The photo was captured at an angle — 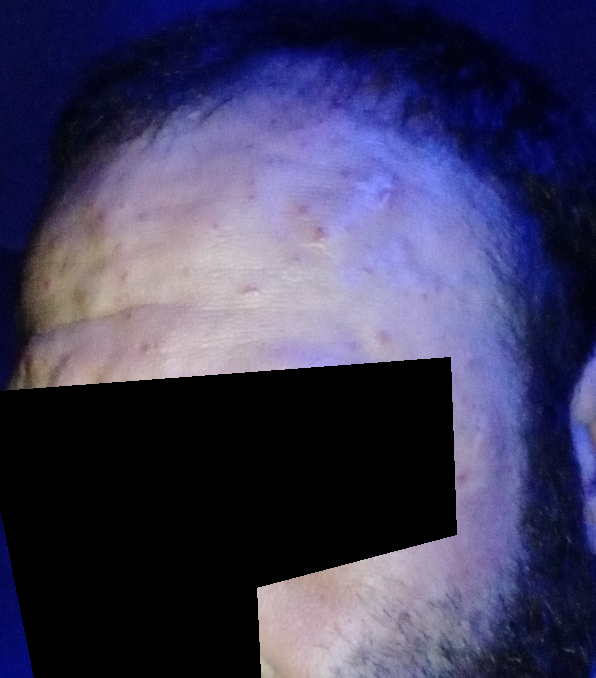<dermatology_case>
<assessment>not assessable</assessment>
</dermatology_case>